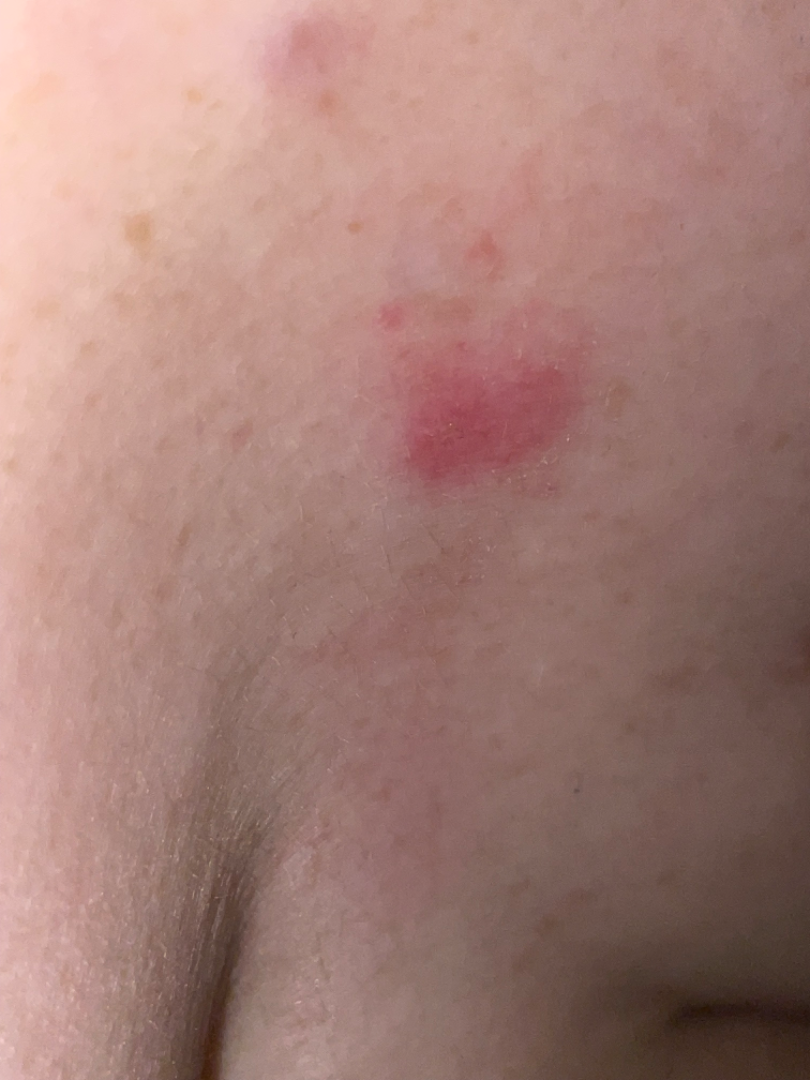assessment=unable to determine | image framing=at an angle | onset=less than one week | patient's own categorization=a rash | associated systemic symptoms=joint pain.